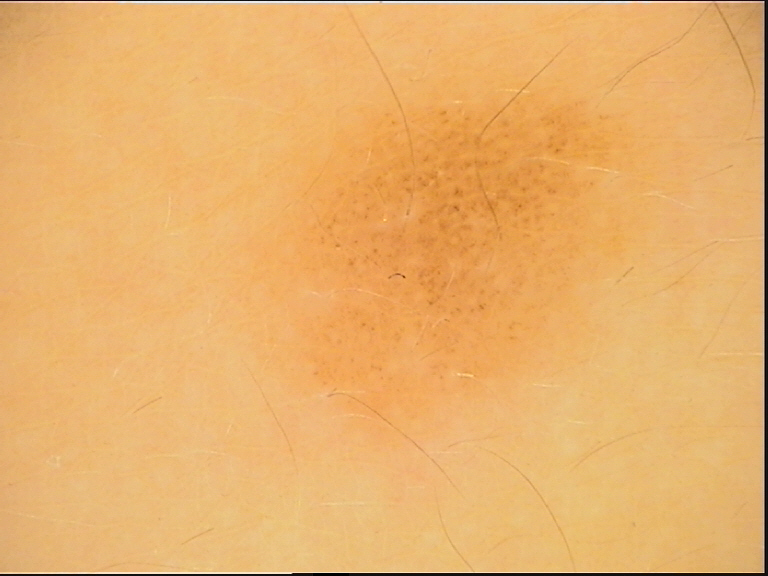modality: dermoscopy, class: dysplastic junctional nevus (expert consensus).